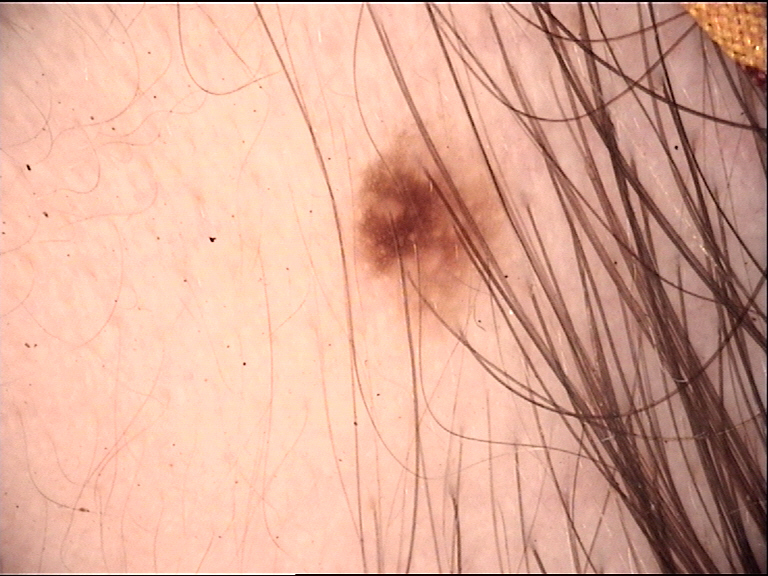image = dermatoscopy; subtype = compound, banal; class = Miescher nevus (expert consensus).